The patient is a female aged 40–49. The lesion is associated with burning and itching. This image was taken at a distance. The affected area is the top or side of the foot. The patient indicates the condition has been present for about one day: 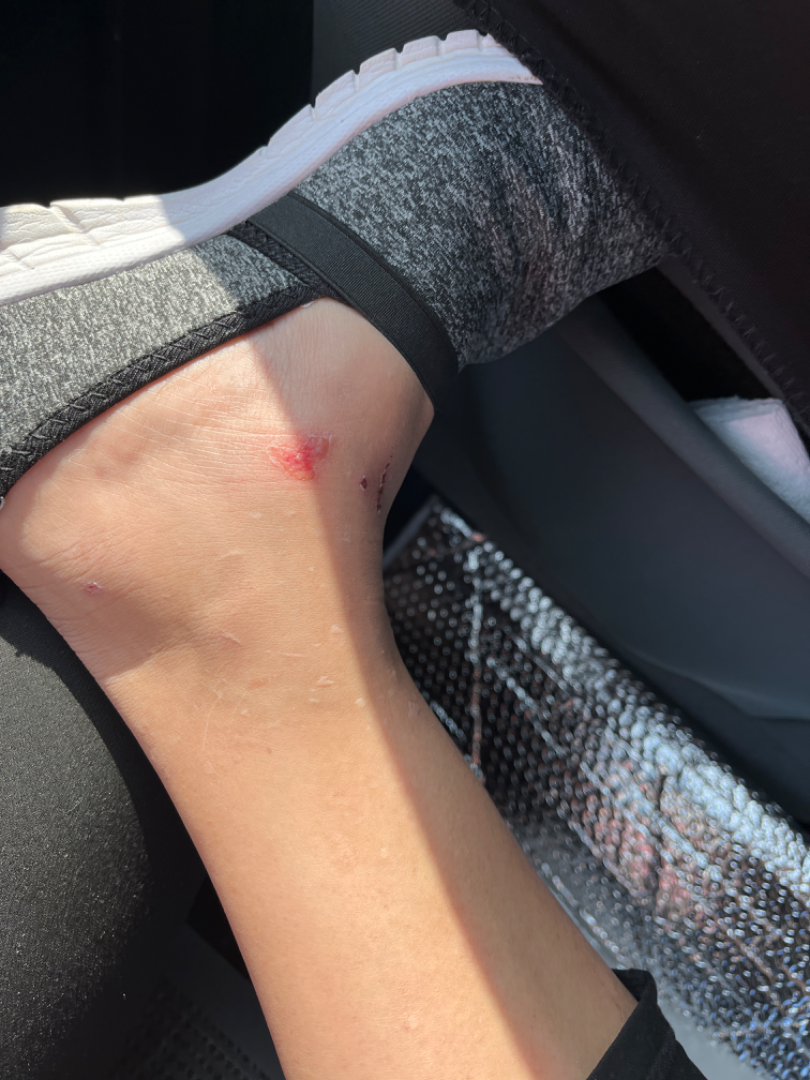The skin condition could not be confidently assessed from this image.